An image taken at a distance — 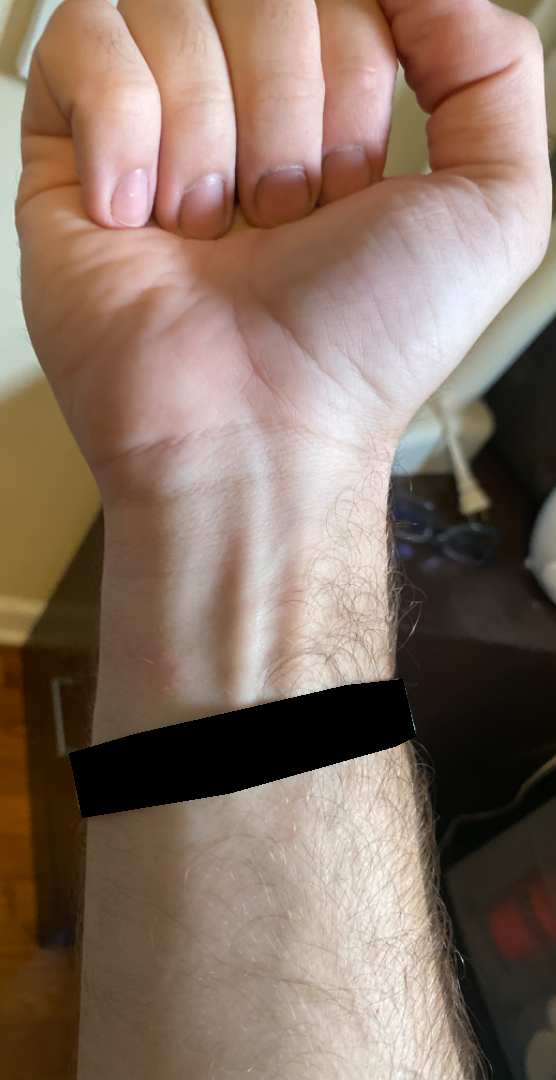<summary>
<differential>Eczema, Allergic Contact Dermatitis, Irritant Contact Dermatitis</differential>
</summary>